A dermoscopy image of a single skin lesion:
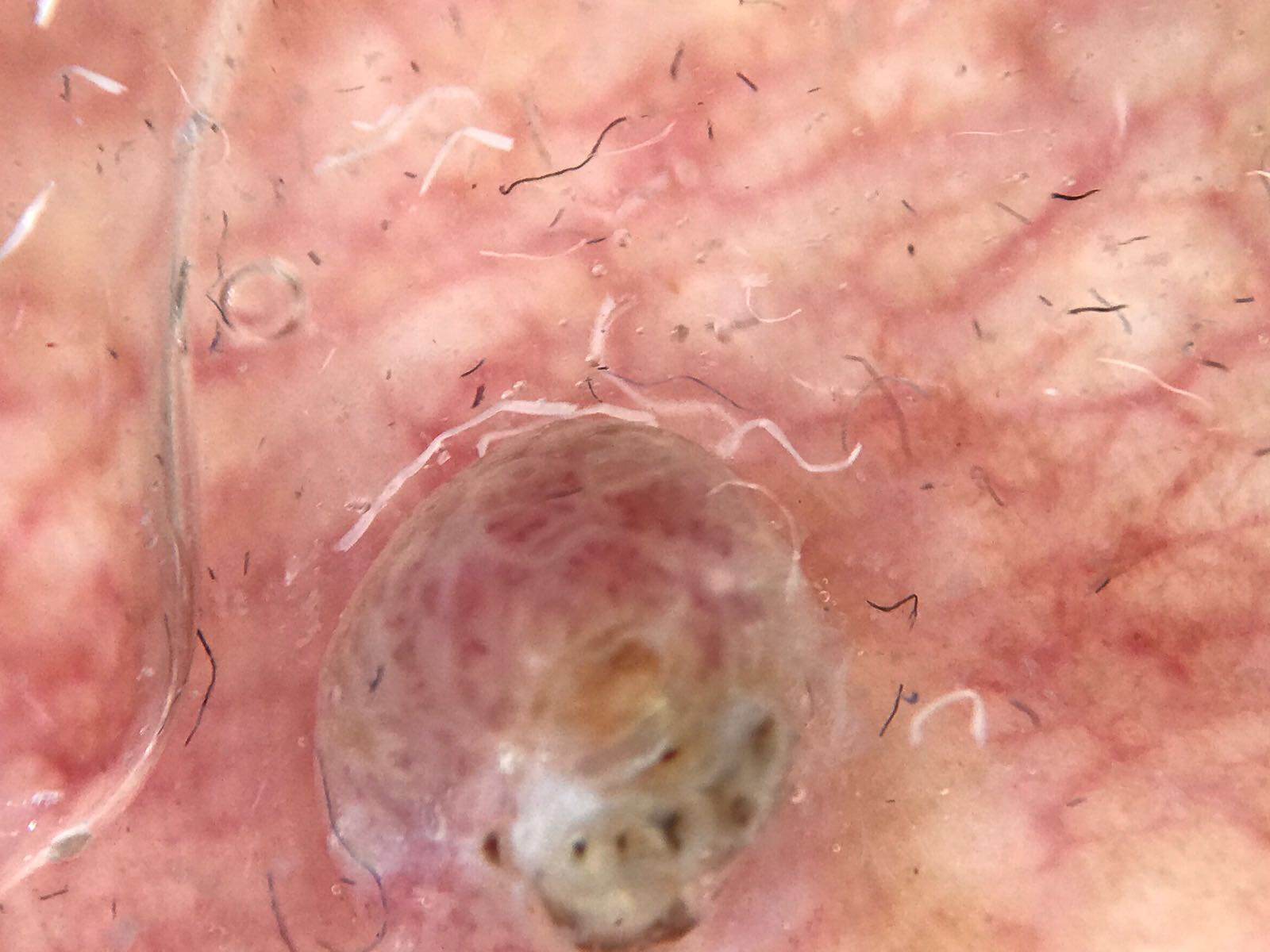Pathology: Biopsy-confirmed as a malignancy — a squamous cell carcinoma.